The patient indicates the lesion is raised or bumpy and flat · skin tone: lay graders estimated a MST of 2 · located on the leg, arm, head or neck and back of the hand · no associated systemic symptoms reported · this is a close-up image.
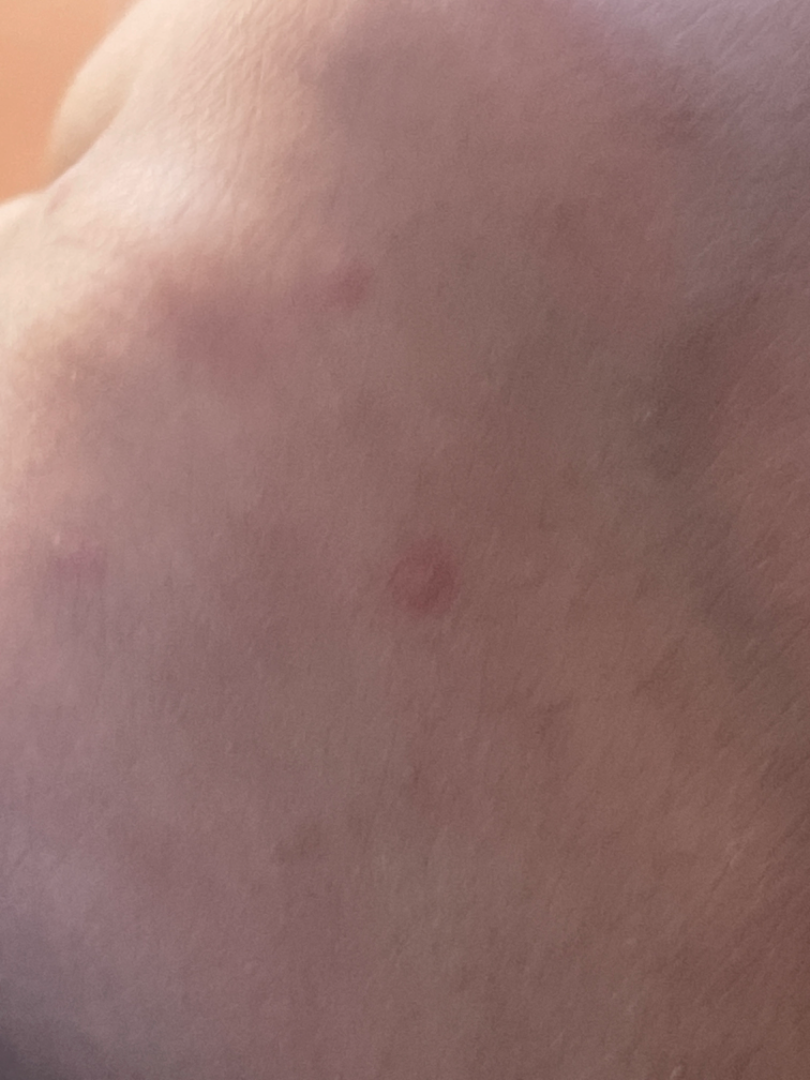Case summary:
- assessment — ungradable on photographic review